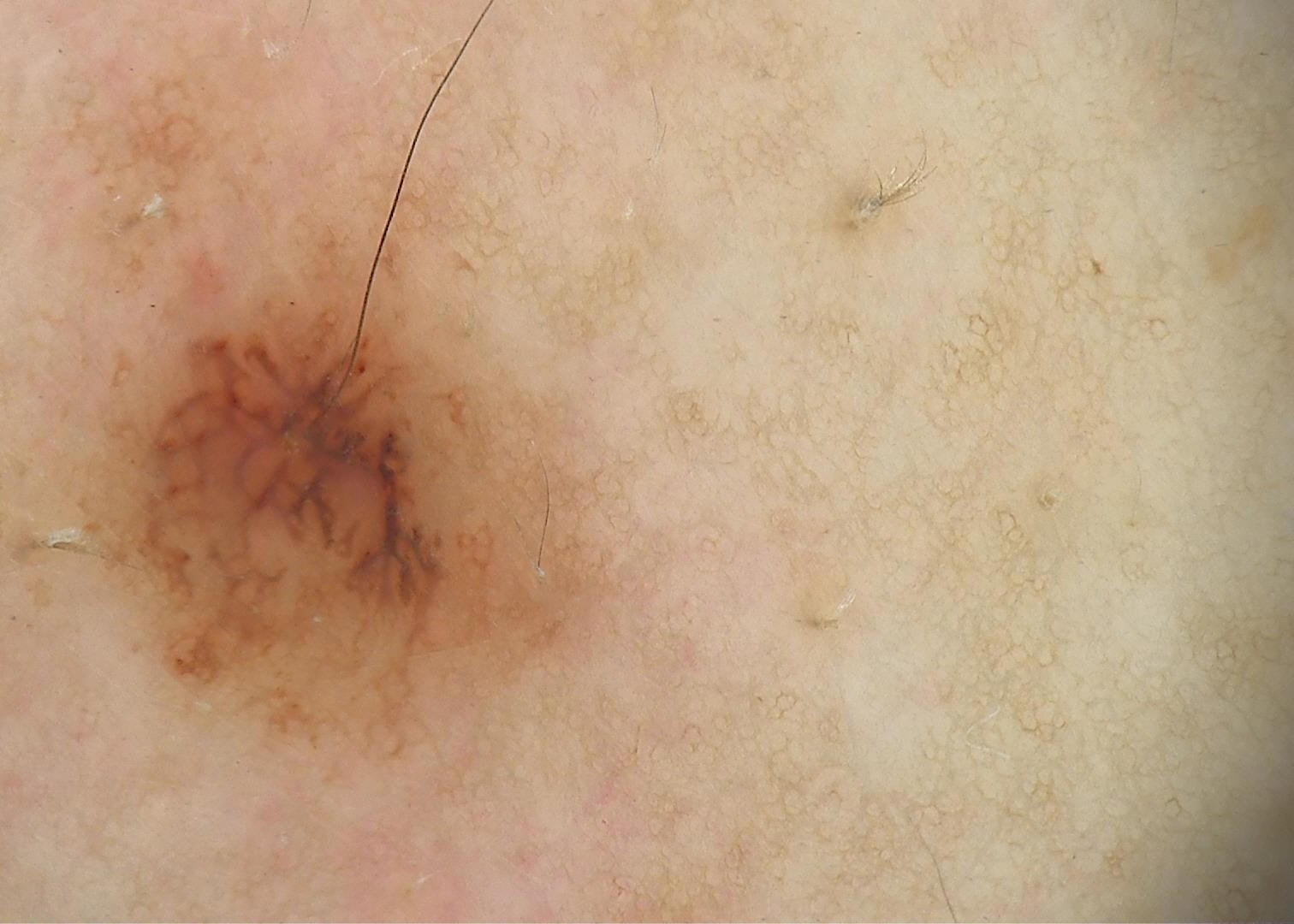Findings:
* label: dermal nevus (expert consensus)